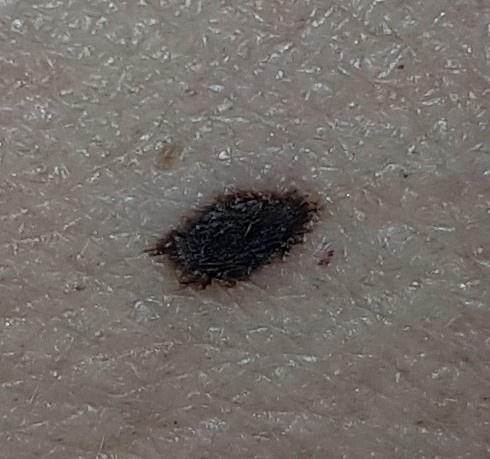{"diagnosis": {"name": "Nevus", "malignancy": "benign", "confirmation": "histopathology", "lineage": "melanocytic"}}